A dermoscopy image of a single skin lesion.
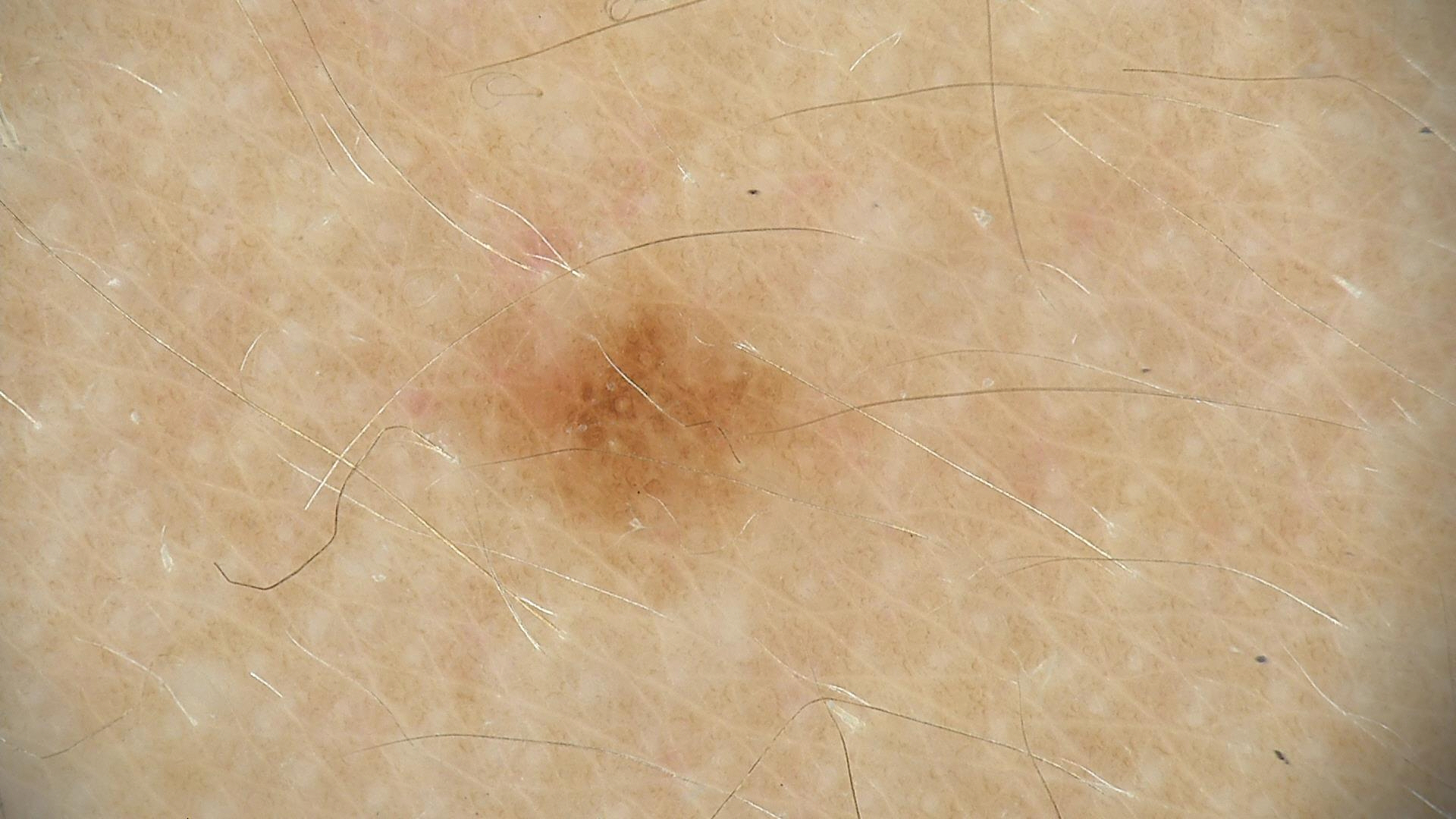Consistent with a dysplastic junctional nevus.